Located on the arm, leg, front of the torso, back of the torso and top or side of the foot · skin tone: Fitzpatrick skin type III; human graders estimated Monk skin tone scale 3 or 5 (two reviewer pools disagreed) · male contributor, age 40–49 · the photograph was taken at a distance · the patient described the issue as a rash · the contributor notes itching.
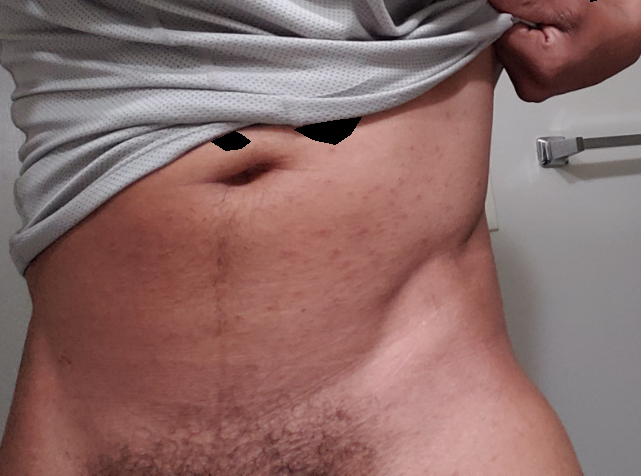Findings: On remote dermatologist review, Folliculitis and Insect Bite were each considered, in no particular order.